A skin lesion imaged with a dermatoscope.
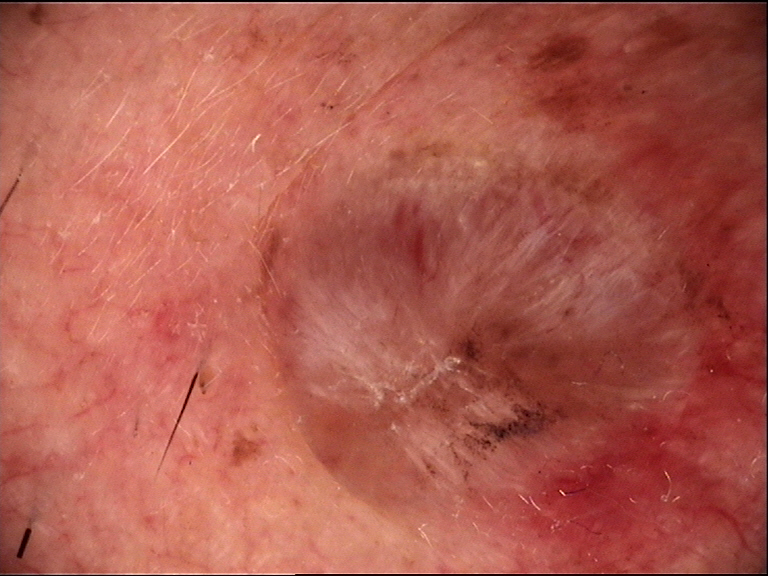The morphology is that of a keratinocytic lesion. Histopathologically confirmed as a basal cell carcinoma.